A dermatoscopic image of a skin lesion.
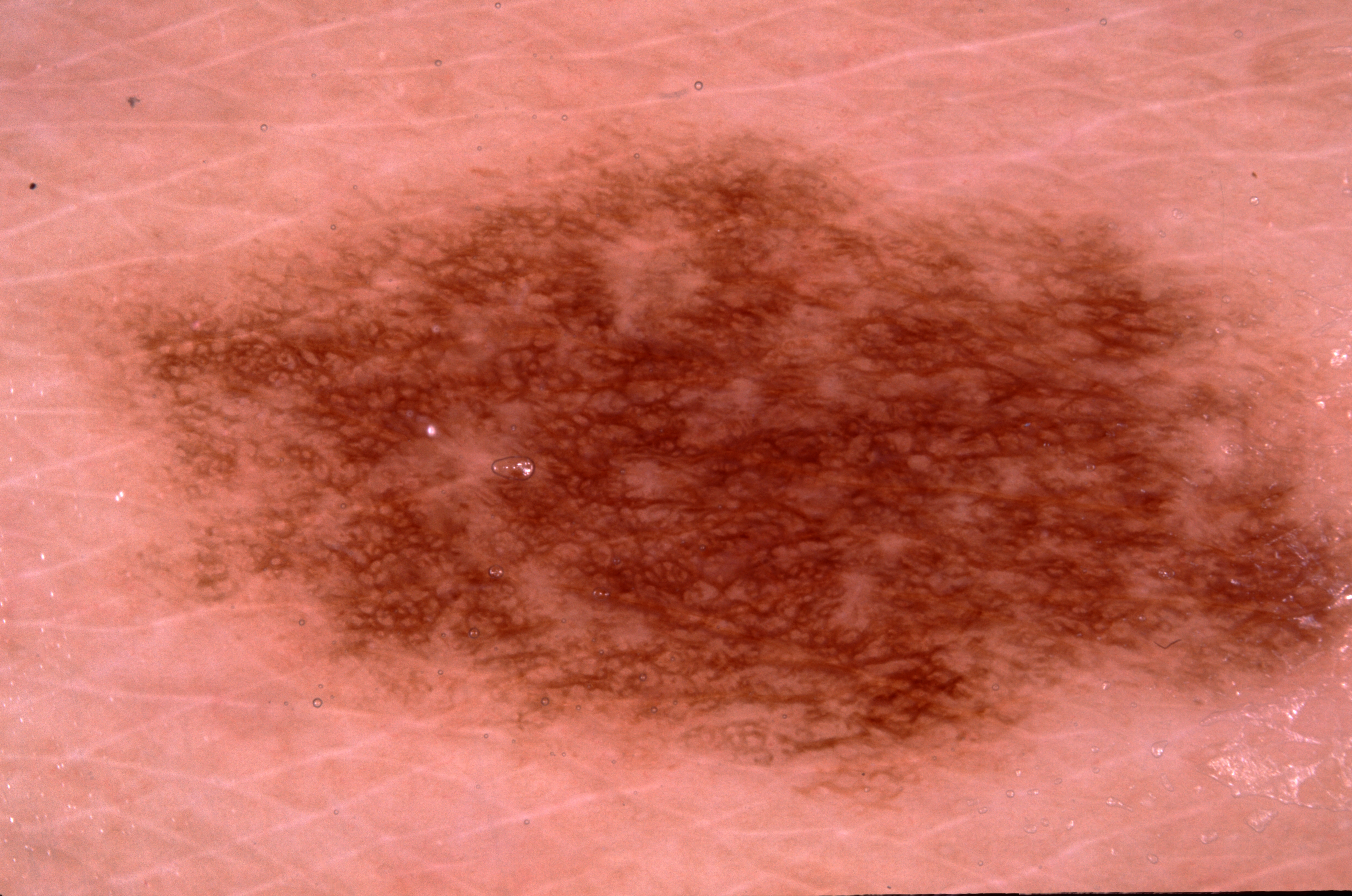• lesion location — [116,147,1341,791]
• features — pigment network; absent: milia-like cysts, streaks, and negative network
• diagnosis — a melanocytic nevus